The patient is male, the lesion involves the leg, the contributor reports the lesion is rough or flaky and raised or bumpy, the photograph is a close-up of the affected area, the contributor reports the condition has been present for less than one week, the patient described the issue as a rash: 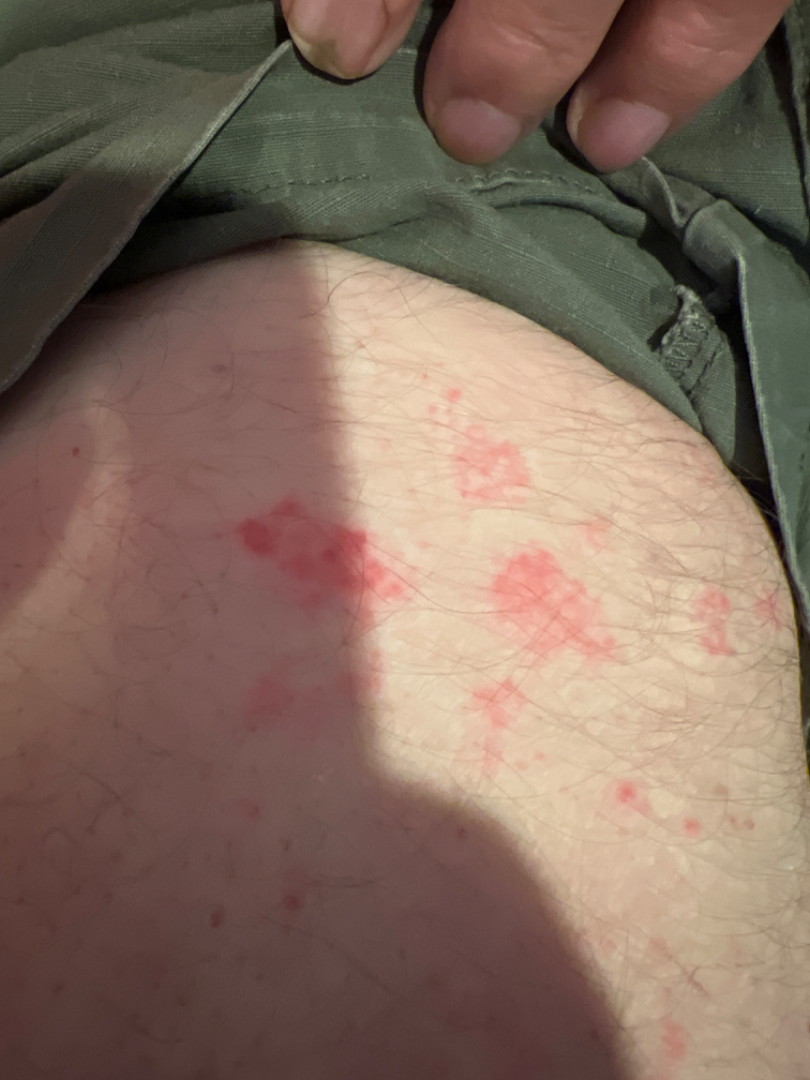The reviewer was unable to grade this case for skin condition.